The photo was captured at a distance; male subject, age 18–29; the leg is involved: 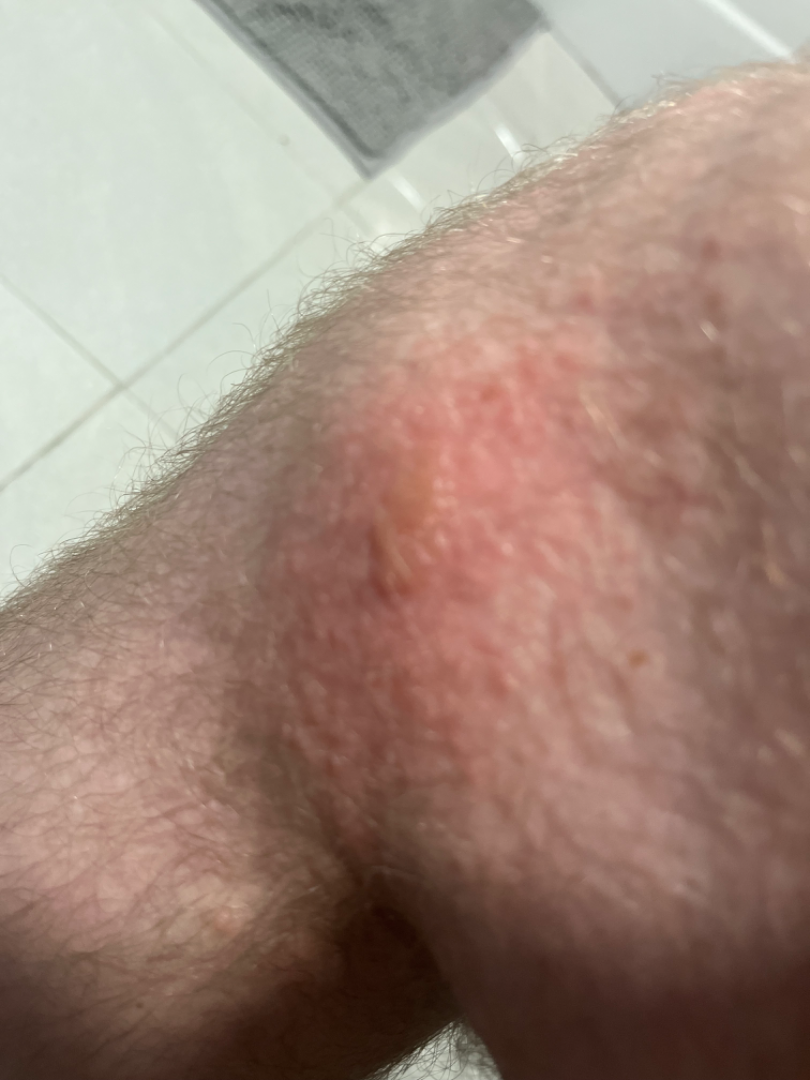Q: Reported symptoms?
A: burning and itching
Q: How does the lesion feel?
A: raised or bumpy and fluid-filled
Q: Duration?
A: less than one week
Q: Patient's own categorization?
A: a rash
Q: What is the differential diagnosis?
A: the impression is Insect Bite